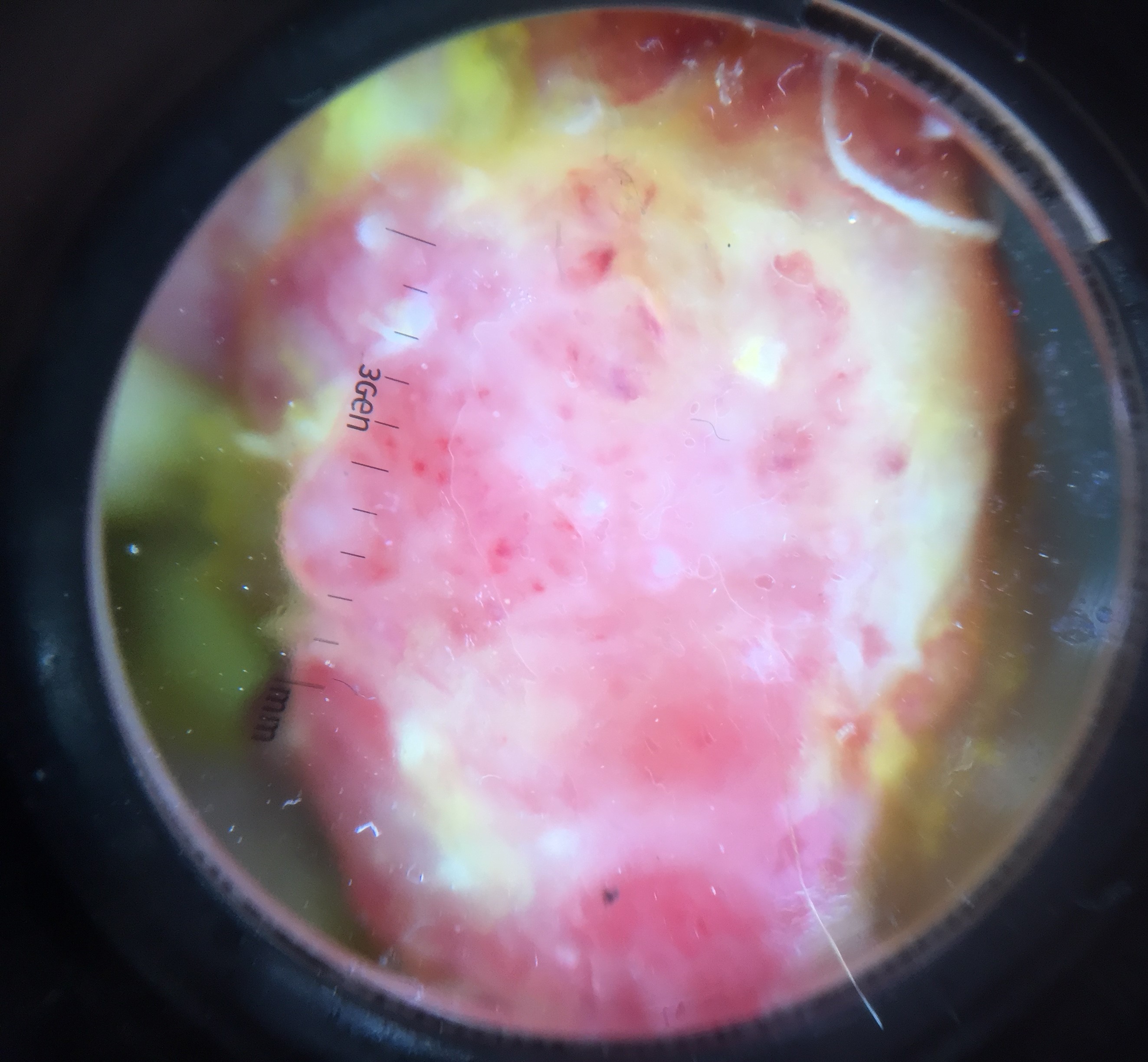Findings:
* diagnostic label — acral nodular melanoma (biopsy-proven)